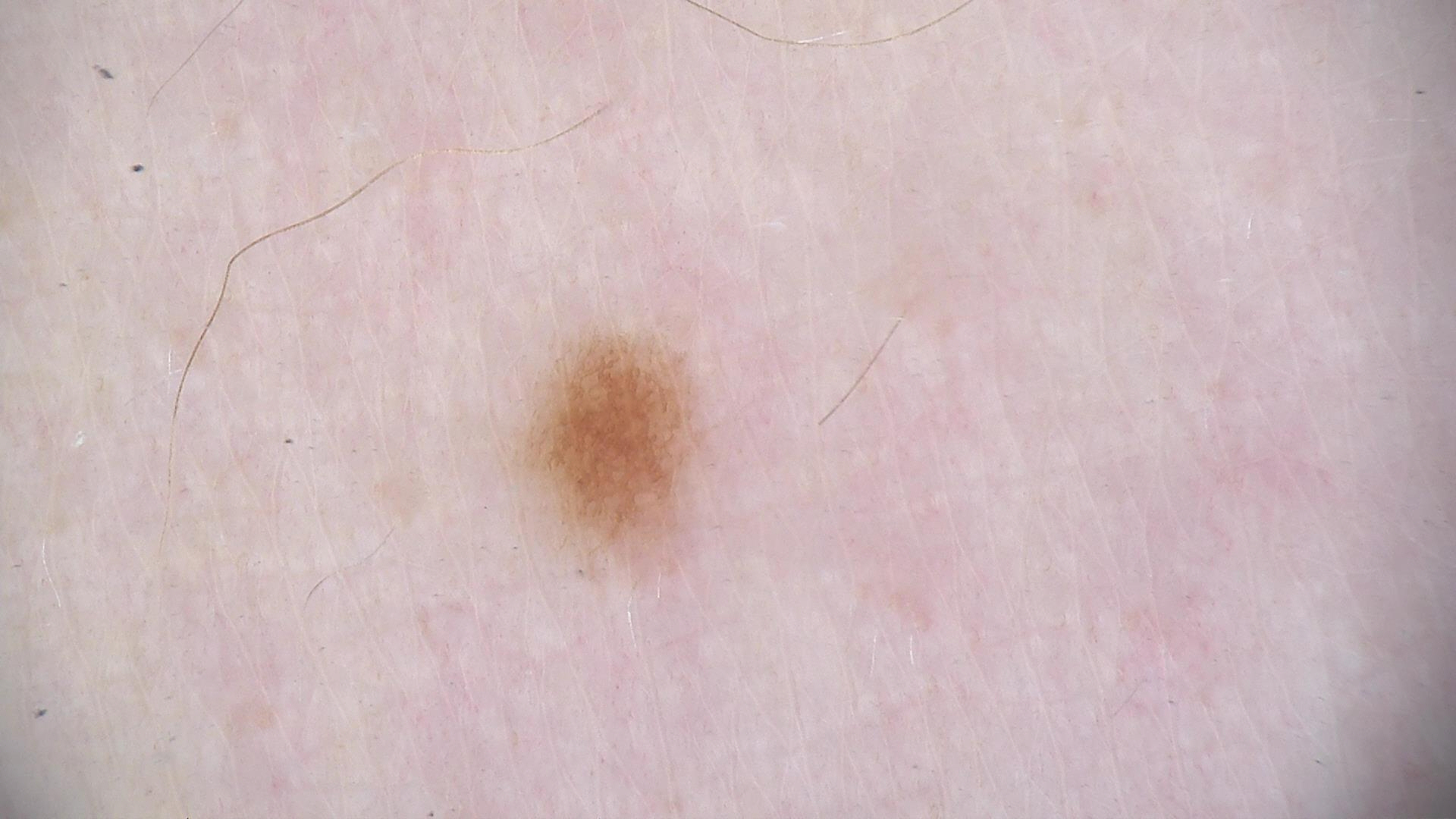Case:
• imaging · dermatoscopy
• classification · banal
• diagnostic label · junctional nevus (expert consensus)